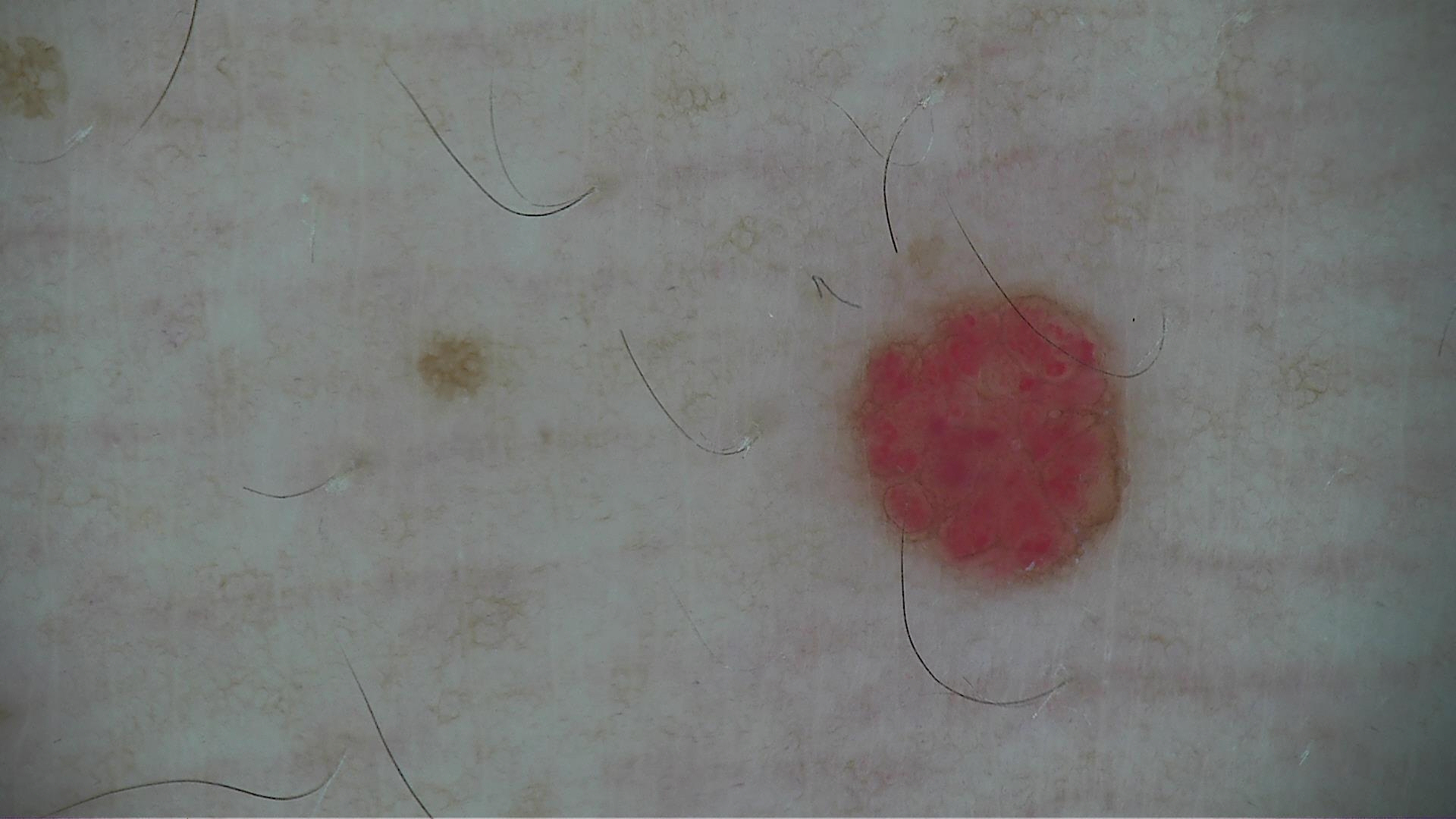A dermatoscopic image of a skin lesion.
The architecture is that of a vascular lesion.
Classified as a hemangioma.